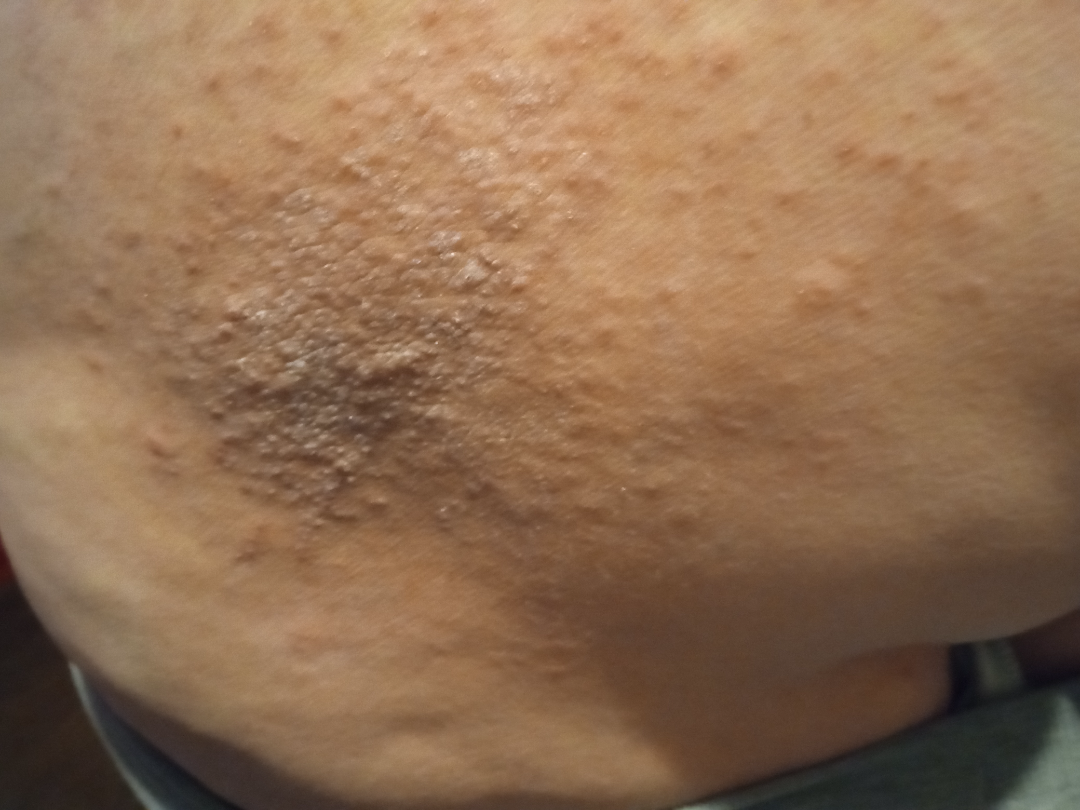An image taken at a distance. Psoriasis and Lichen Simplex Chronicus were each considered, in no particular order.